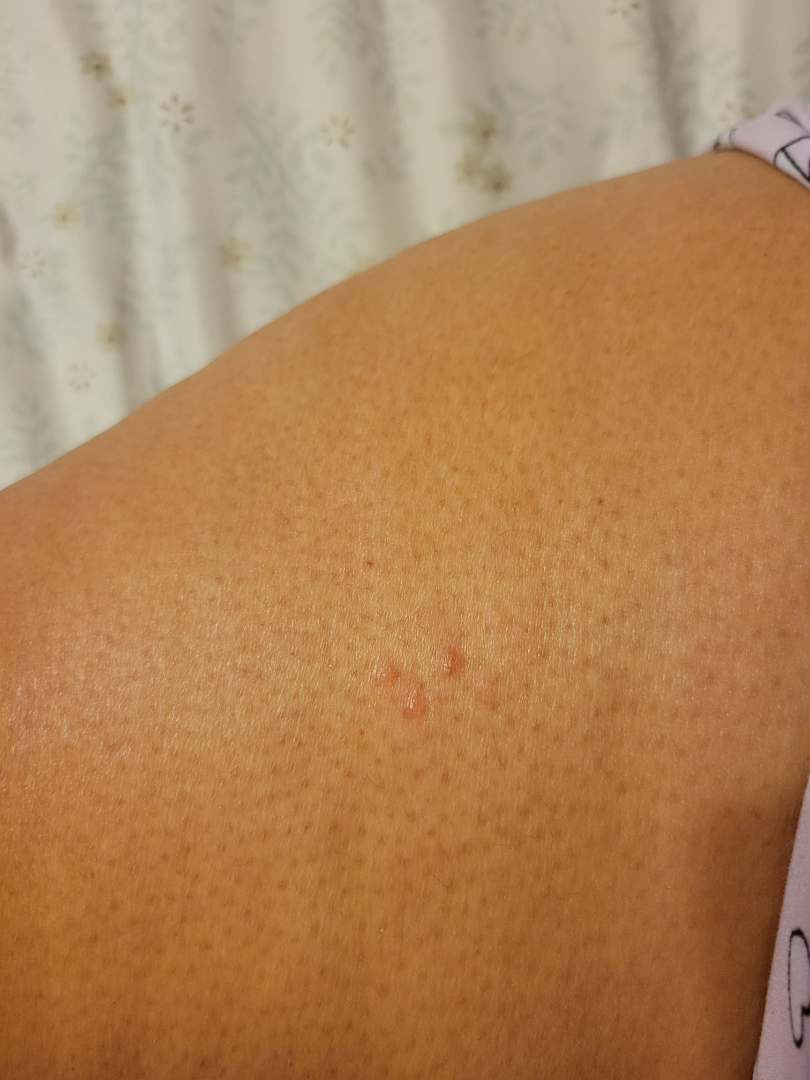Q: What conditions are considered?
A: three independent reviewers: Folliculitis and Insect Bite were considered with similar weight; less probable is Allergic Contact Dermatitis; less likely is Herpes Simplex